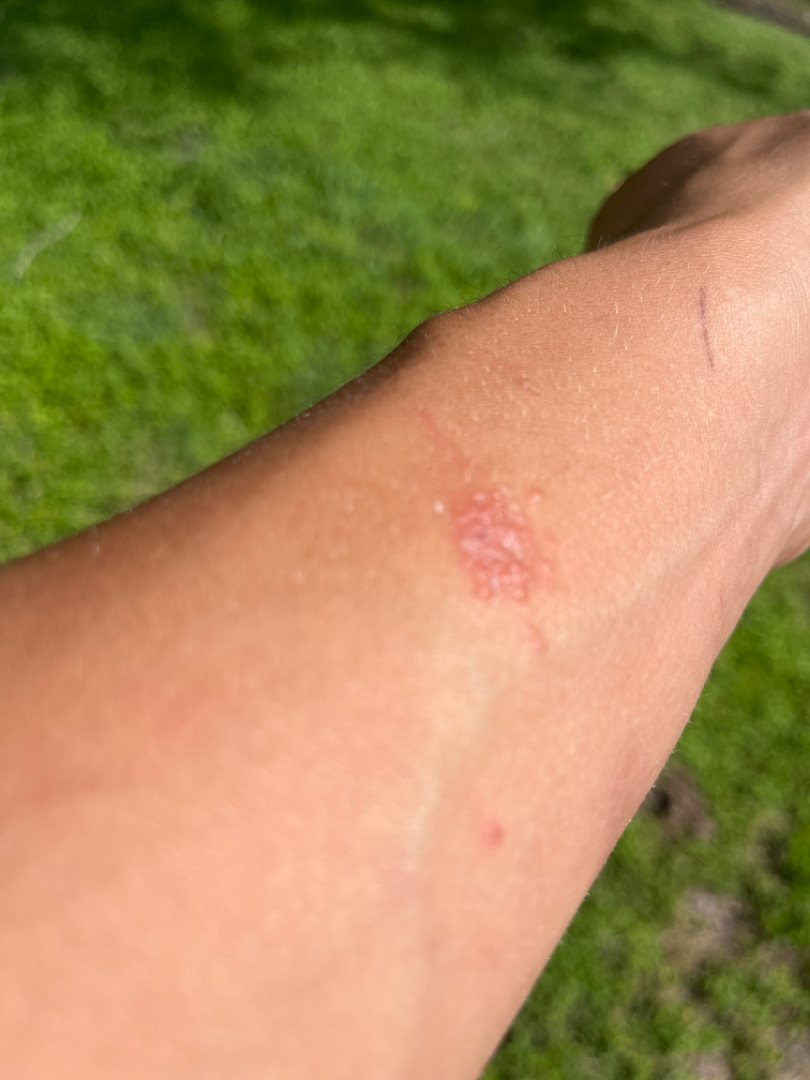Q: What was the assessment?
A: not assessable
Q: What is the framing?
A: at an angle